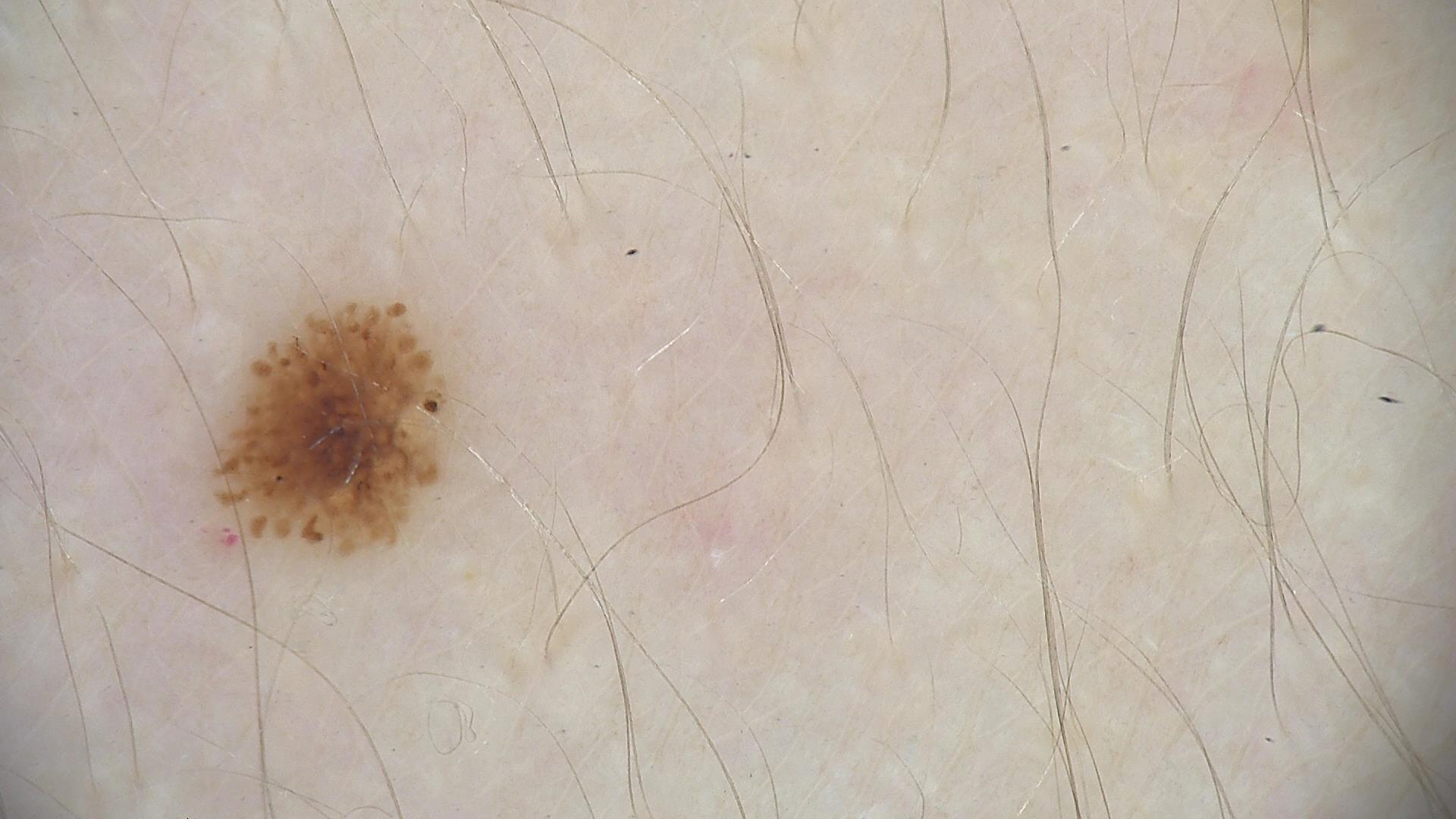Conclusion:
Labeled as a dysplastic junctional nevus.